The photo was captured at an angle · female subject, age 50–59 · the front of the torso and back of the torso are involved: 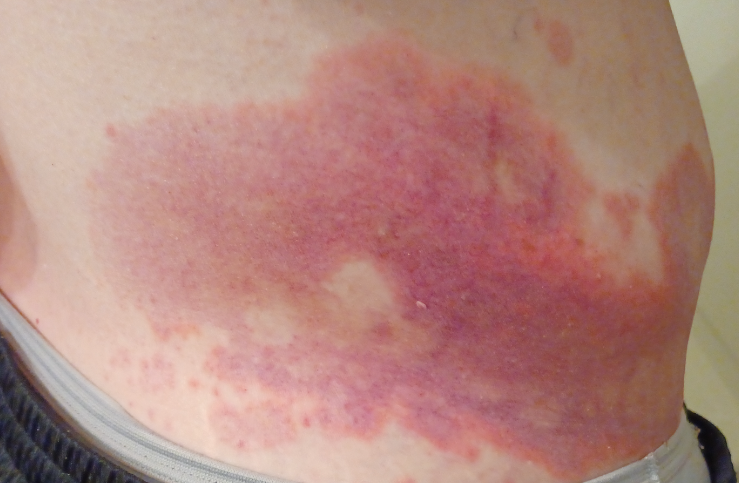Notes:
* assessment · not assessable
* patient's own categorization · a rash
* lesion symptoms · bothersome appearance, enlargement and darkening
* surface texture · flat
* onset · less than one week
* constitutional symptoms · none reported